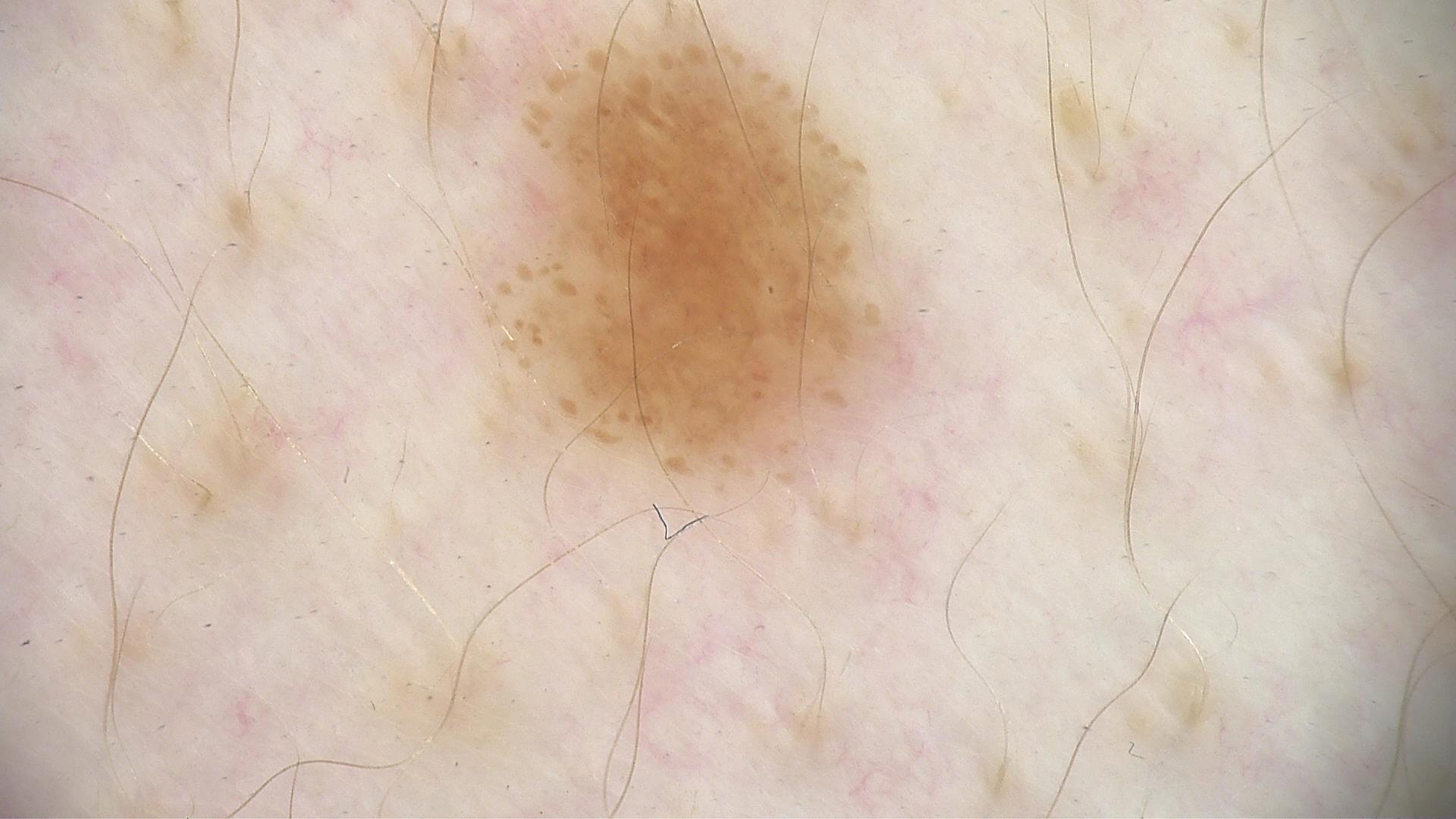{"image": "dermatoscopy", "diagnosis": {"name": "dysplastic junctional nevus", "code": "jd", "malignancy": "benign", "super_class": "melanocytic", "confirmation": "expert consensus"}}